The patient is 18–29, male; close-up view; the palm, back of the hand, leg and top or side of the foot are involved.
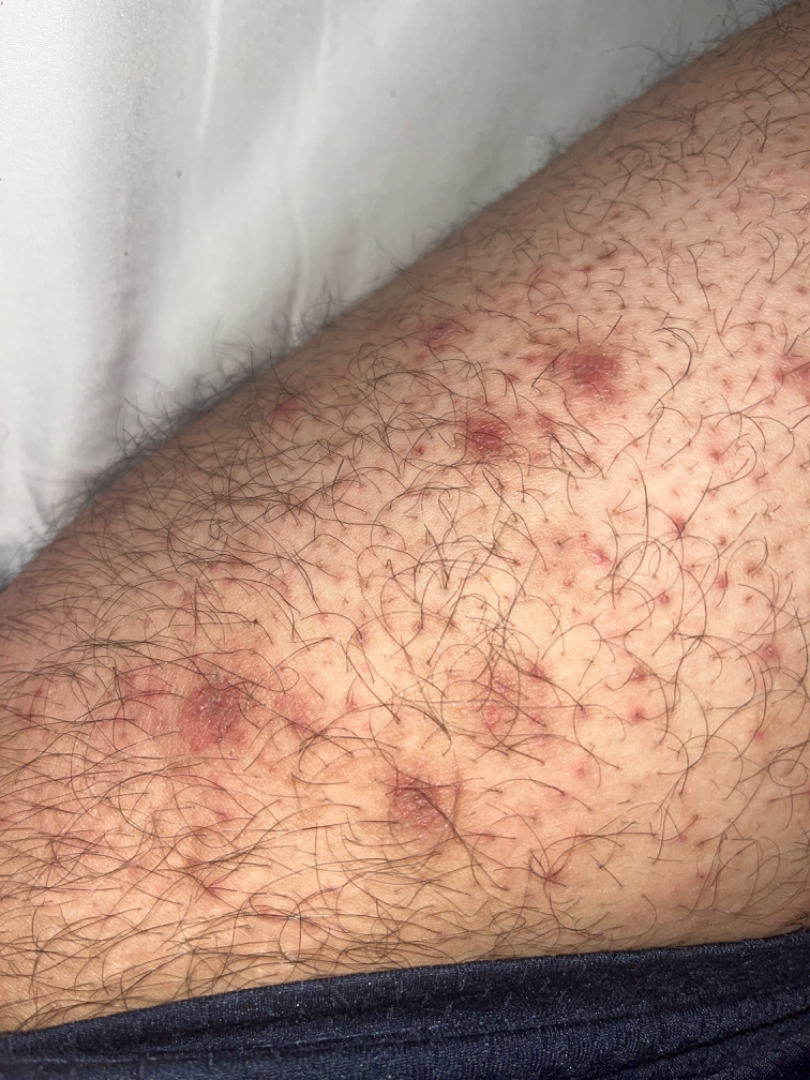On dermatologist assessment of the image, Folliculitis (0.33); Psoriasis (0.33); Eczema (0.33).